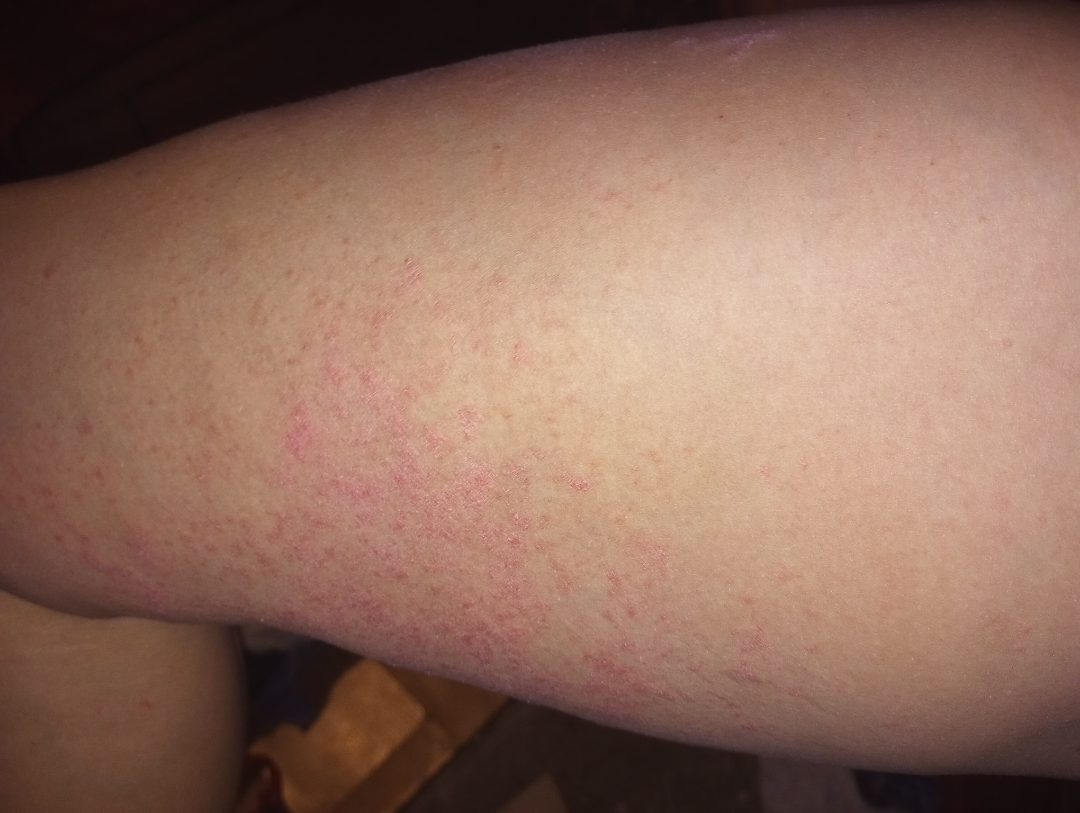Notes:
• reported symptoms — enlargement and bothersome appearance
• image framing — close-up
• site — back of the torso, arm and leg
• described texture — raised or bumpy
• patient describes the issue as — a rash
• onset — one to four weeks
• skin tone — lay reviewers estimated a Monk skin tone scale of 3
• dermatologist impression — most likely Eczema; also consider Psoriasis